The lesion involves the top or side of the foot, palm and arm · the photograph is a close-up of the affected area · the patient is female — 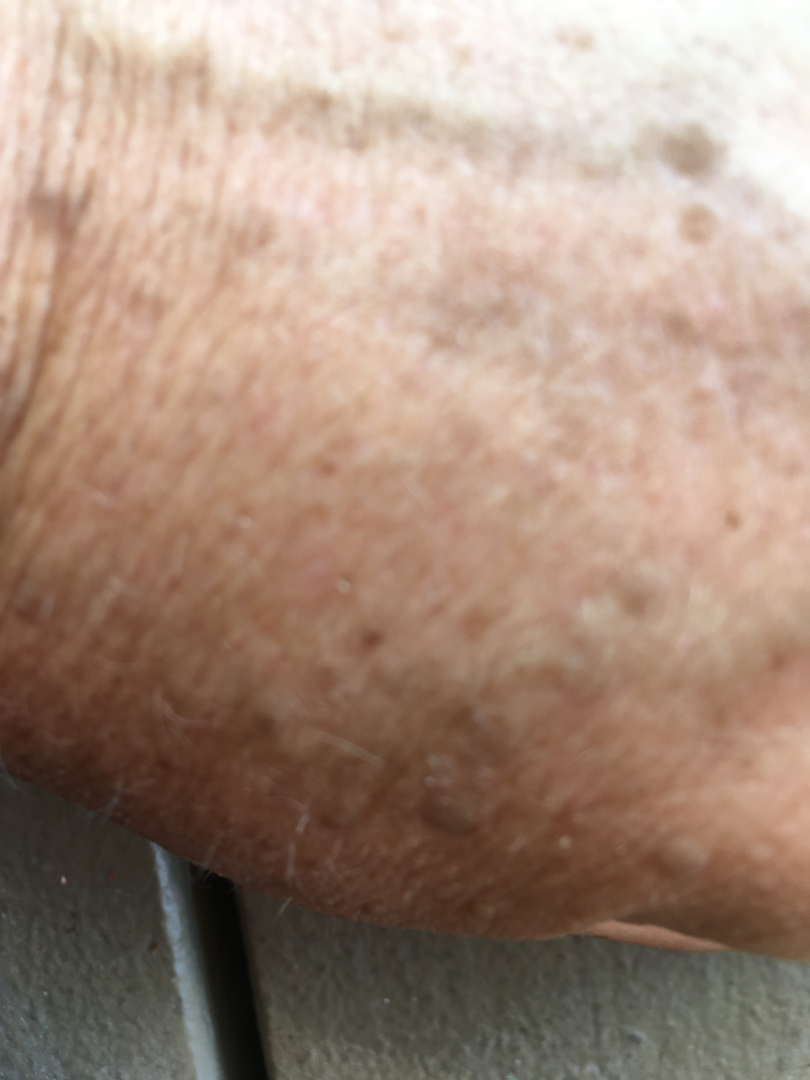– patient's own categorization: a pigmentary problem
– history: more than one year
– described texture: rough or flaky and raised or bumpy
– symptoms: enlargement and bothersome appearance
– other reported symptoms: joint pain and fatigue
– dermatologist impression: SK/ISK (0.67); Lentigo (0.33)